Self-categorized by the patient as a rash, the photograph is a close-up of the affected area, the lesion involves the arm and head or neck, the lesion is associated with itching, reported duration is about one day.
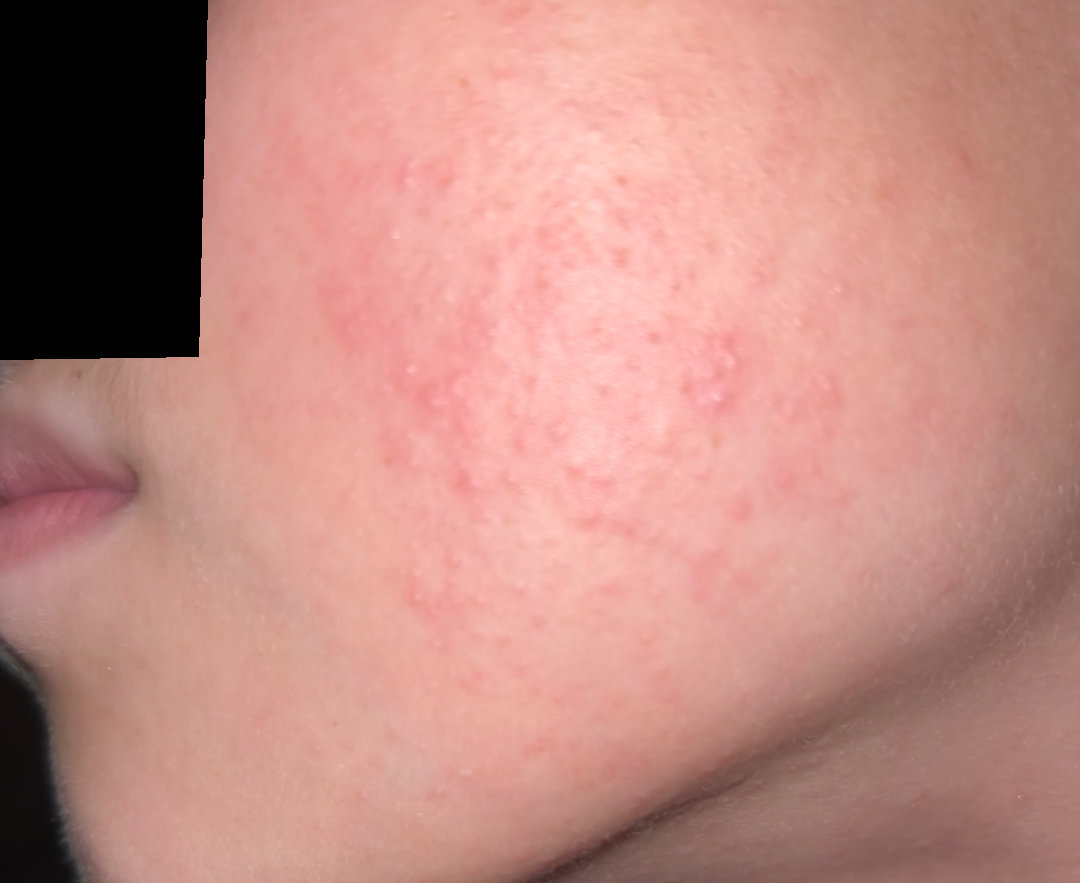differential — the leading impression is Keratosis pilaris; with consideration of Acne.